A dermoscopy image of a single skin lesion; a female subject, approximately 40 years of age — 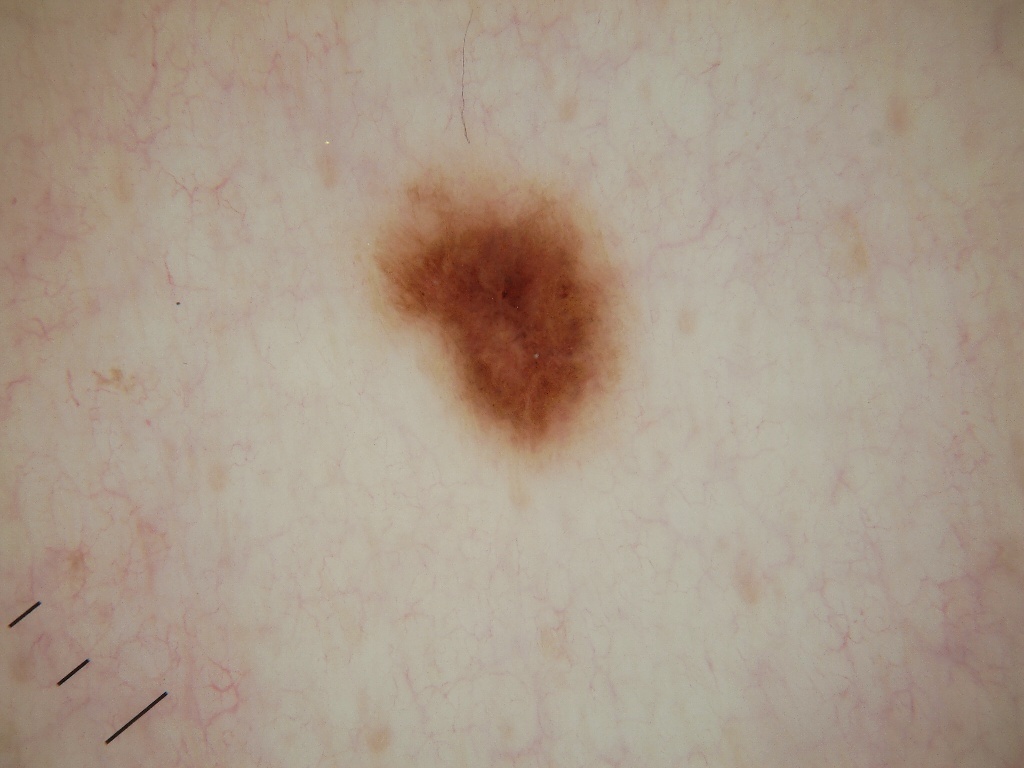A small lesion within a wider field of skin. As (left, top, right, bottom), the lesion occupies the region (355, 153, 628, 457). Dermoscopic assessment notes negative network and milia-like cysts; no globules, streaks, or pigment network. Diagnosed as a melanocytic nevus.